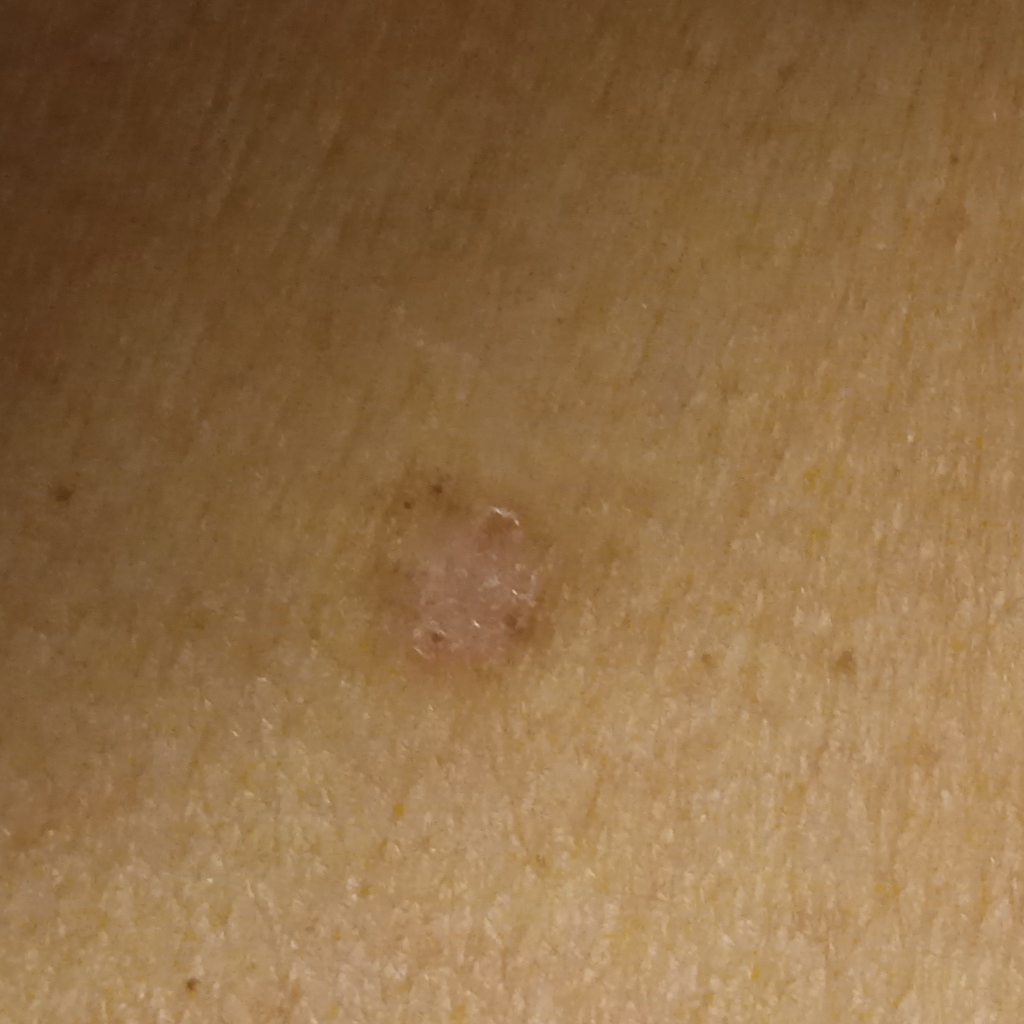Findings:
The referring clinician suspected basal cell carcinoma. On a questionnaire the patient reported a personal history of cancer and a family history of skin cancer. A macroscopic clinical photograph of a skin lesion. The patient says their skin tans without first burning. A female subject 64 years old. Located on the torso. The lesion measures approximately 8.1 mm.
Diagnosis:
Histopathologically confirmed as a basal cell carcinoma, following a punch biopsy, with tumor thickness 0.6 mm.